A skin lesion imaged with a dermatoscope. A female patient aged approximately 25: 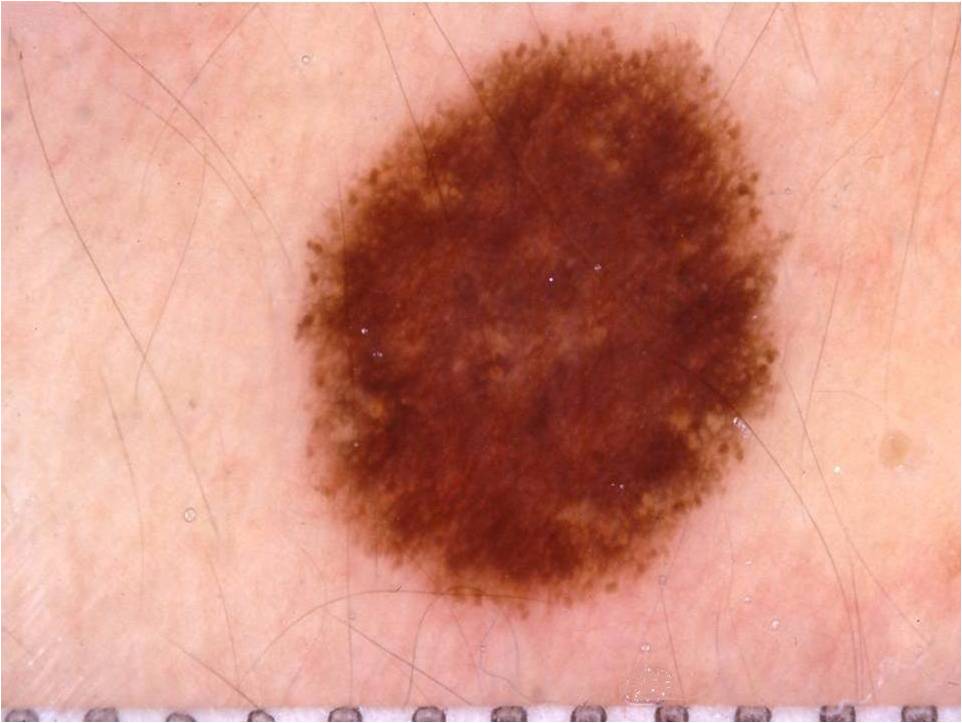Lesion location: left=293, top=24, right=786, bottom=619.
A prominent lesion filling much of the field.
On dermoscopy, the lesion shows globules and pigment network; no negative network, streaks, or milia-like cysts.
Expert review diagnosed this as a melanocytic nevus, a benign lesion.